A dermoscopic close-up of a skin lesion.
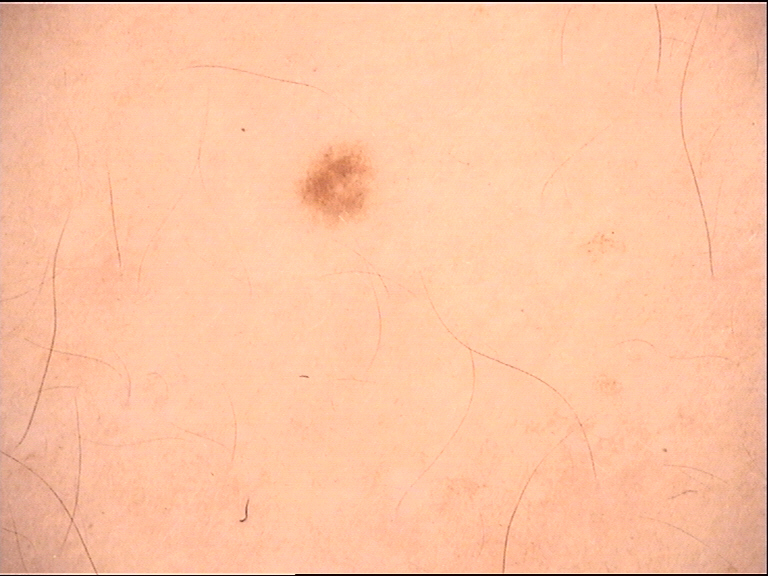assessment: dysplastic junctional nevus (expert consensus)